Dermoscopy of a skin lesion.
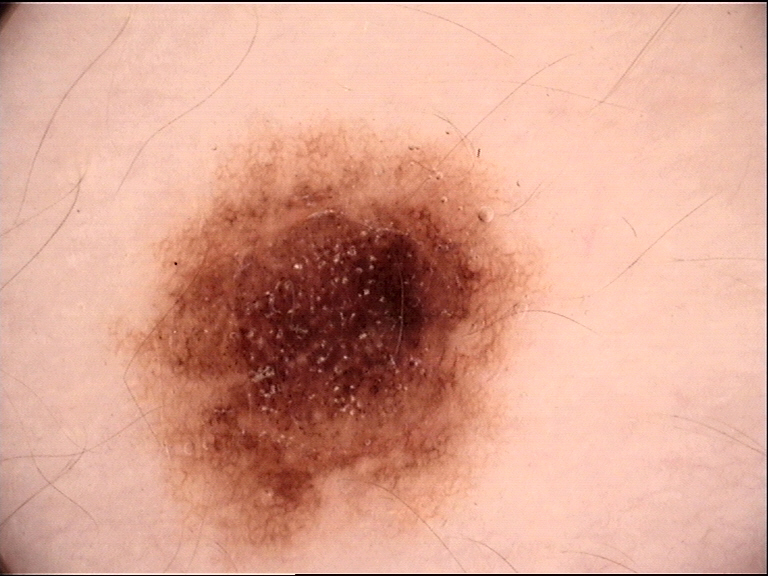<case>
  <diagnosis>
    <name>dysplastic junctional nevus</name>
    <code>jd</code>
    <malignancy>benign</malignancy>
    <super_class>melanocytic</super_class>
    <confirmation>expert consensus</confirmation>
  </diagnosis>
</case>